A dermatoscopic image of a skin lesion:
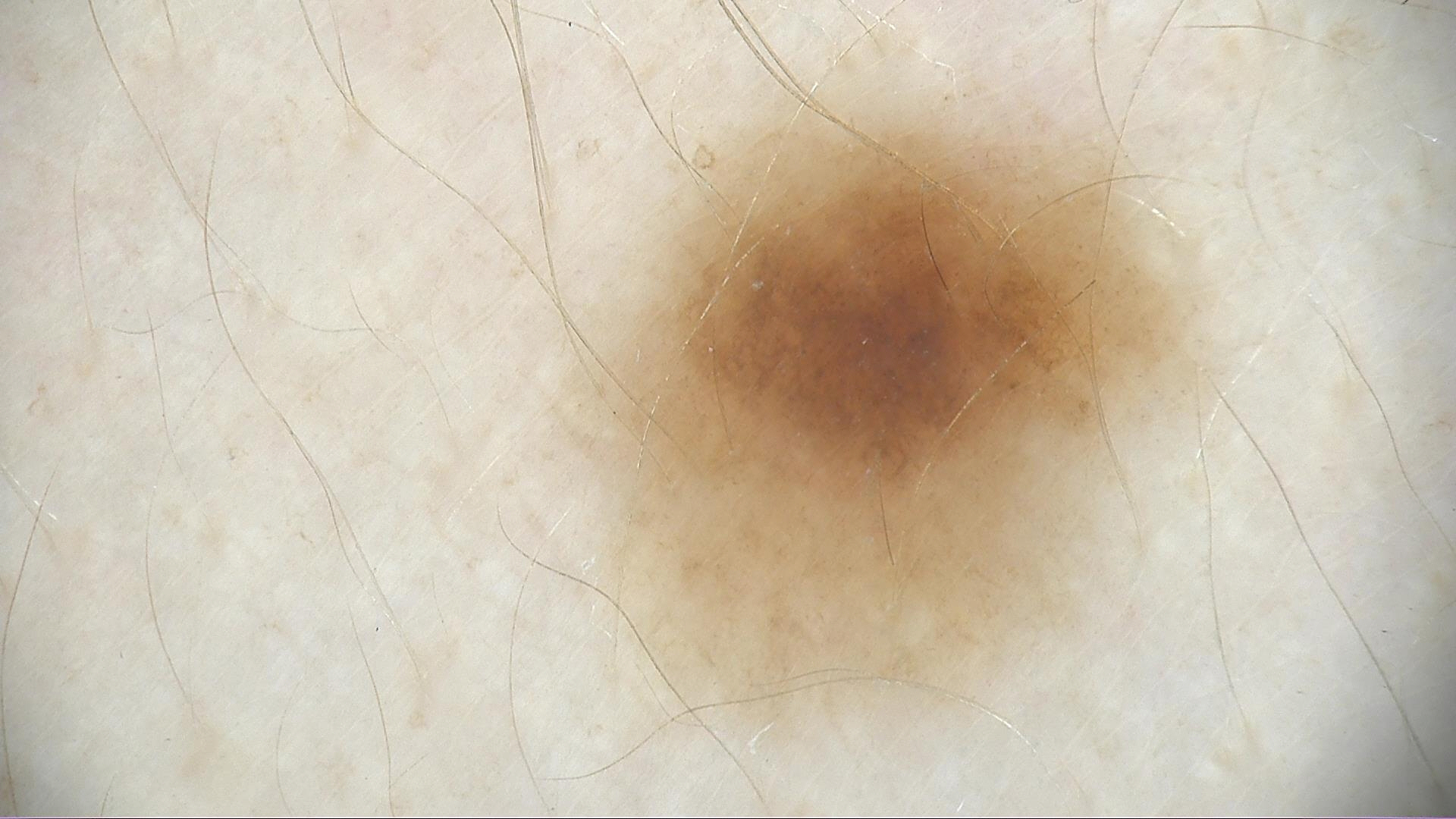Conclusion: The diagnosis was a benign lesion — a dysplastic junctional nevus.